A dermoscopy image of a single skin lesion · a male patient, roughly 50 years of age:
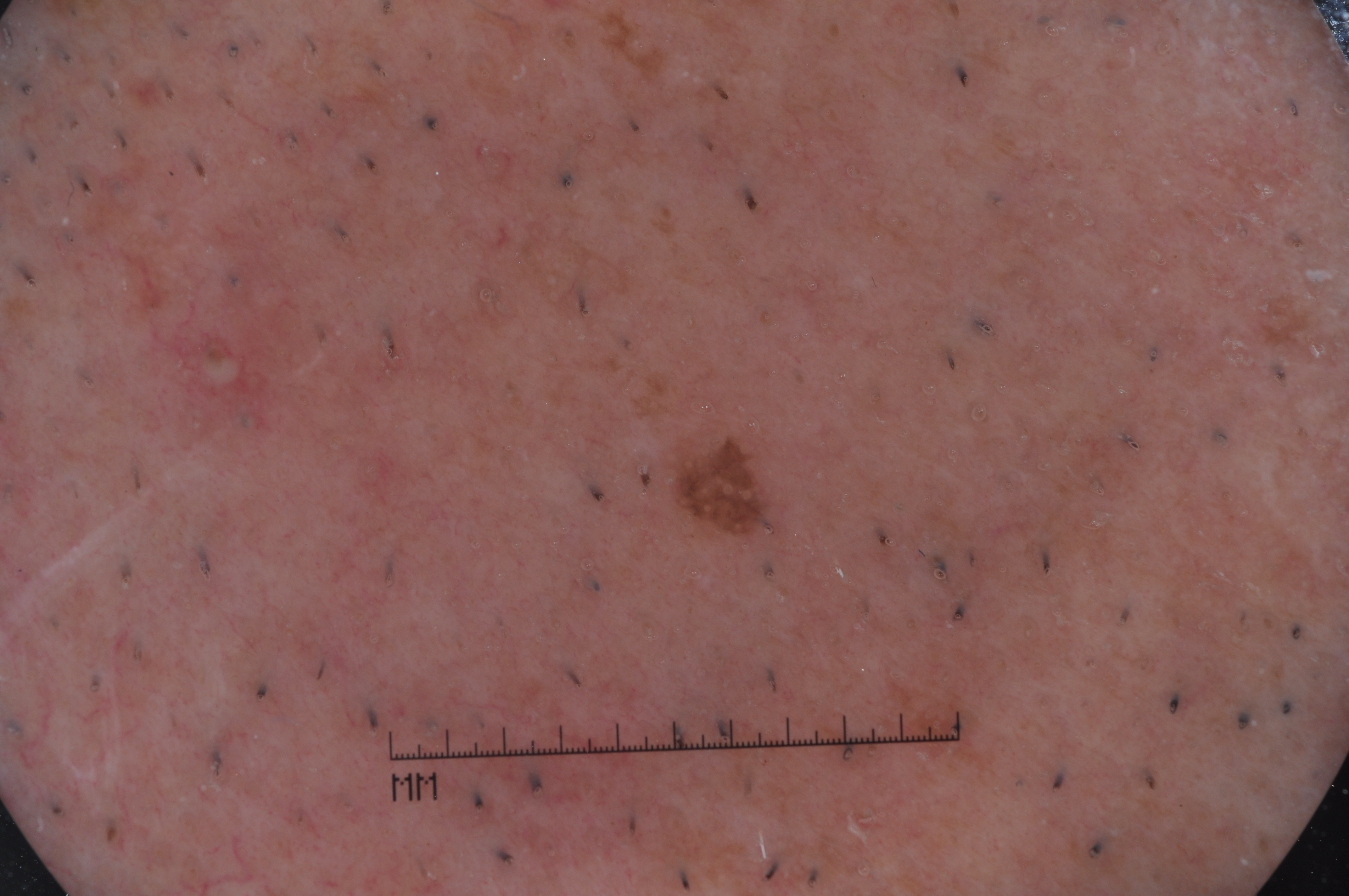– dermoscopic features assessed but absent · streaks, milia-like cysts, negative network, and pigment network
– lesion location · <box>666, 434, 779, 539</box>
– diagnosis · a melanocytic nevus, a benign lesion